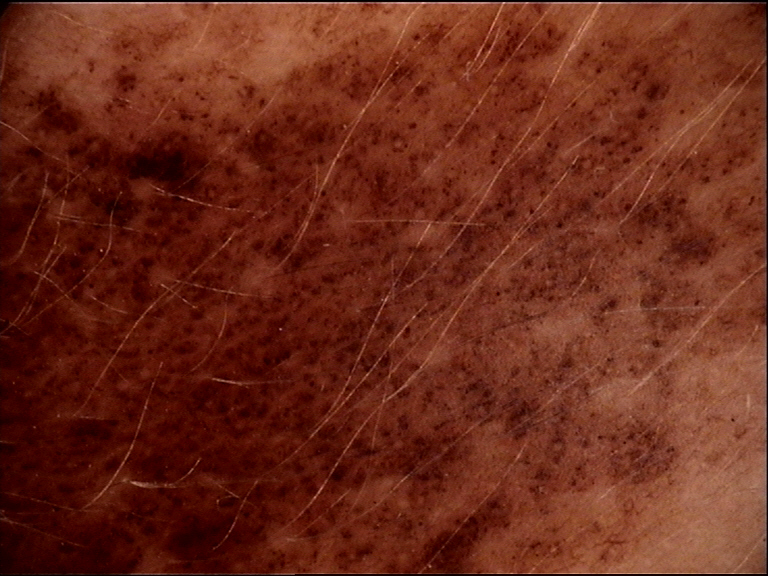A dermoscopic close-up of a skin lesion. The architecture is that of a banal lesion. Diagnosed as a congenital compound nevus.